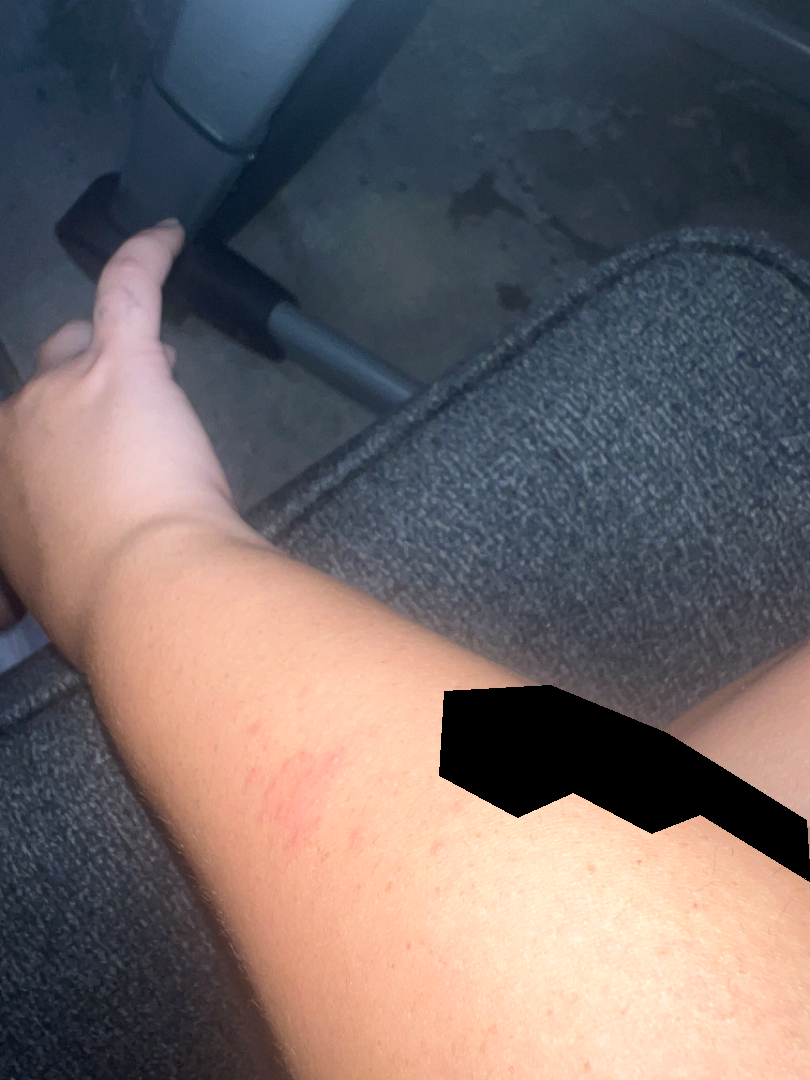Impression: The reviewing dermatologist was unable to assign a differential diagnosis from the image. History: The arm is involved. Texture is reported as fluid-filled and raised or bumpy. The photo was captured at an angle. Reported lesion symptoms include bothersome appearance. Self-reported Fitzpatrick skin type III; non-clinician graders estimated Monk skin tone scale 2 (US pool) or 3 (India pool).